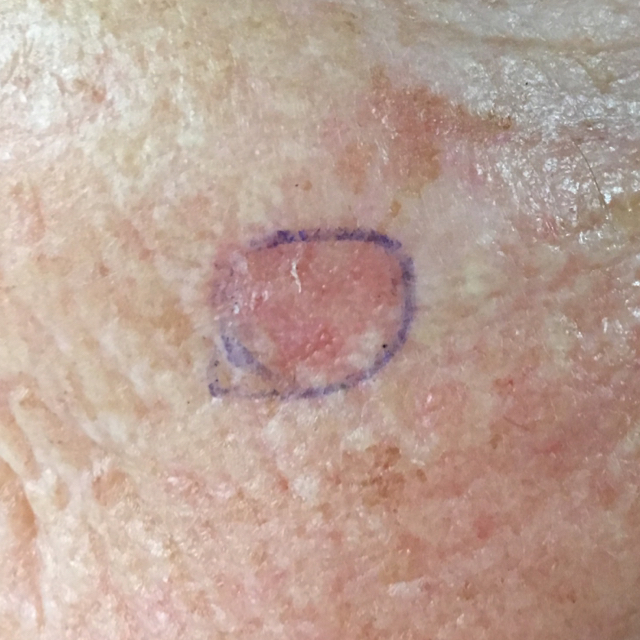A subject age 75.
A clinical close-up photograph of a skin lesion.
The lesion is on the face.
The diagnostic impression was a lesion of indeterminate malignant potential — an actinic keratosis.